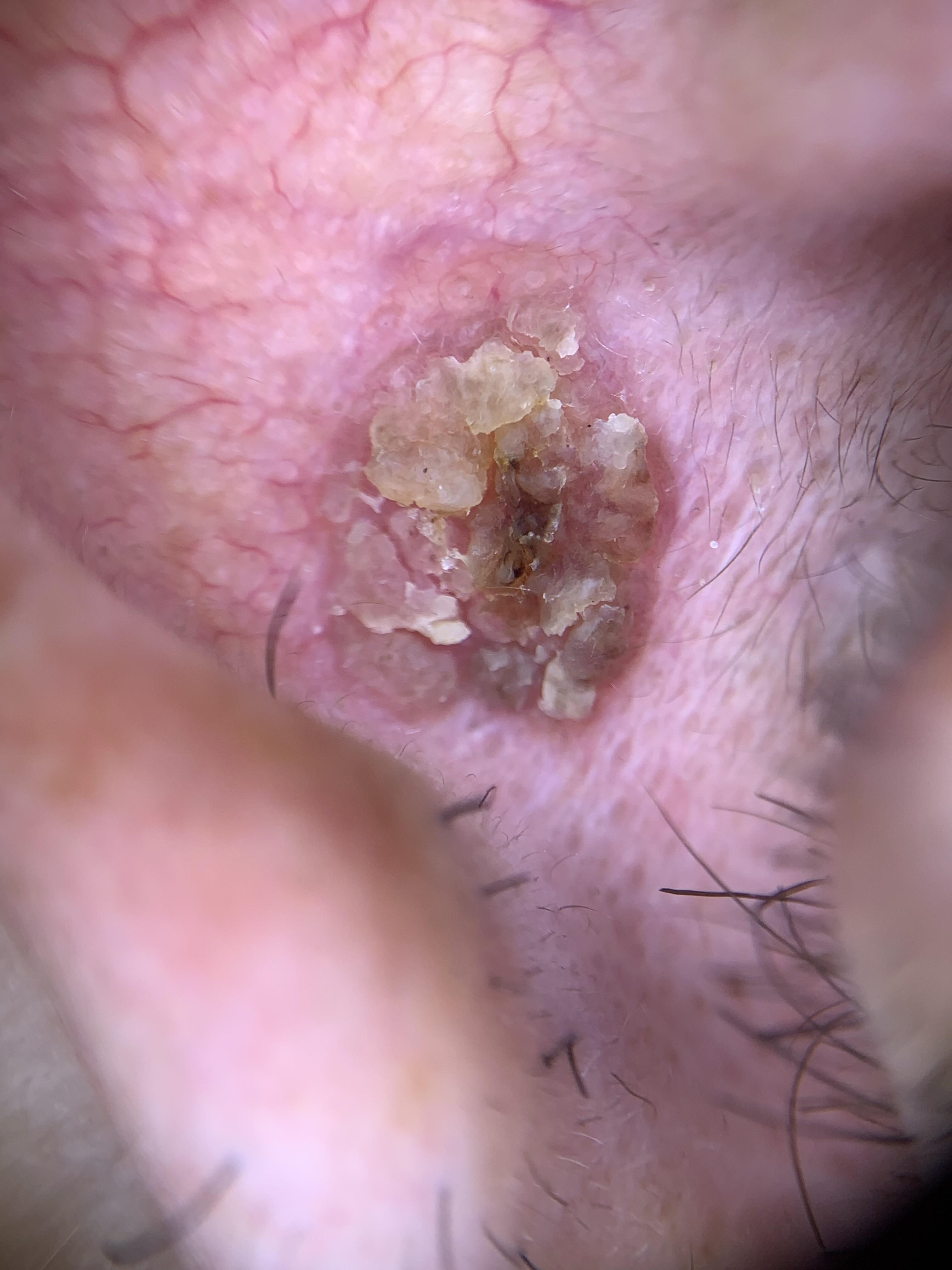patient — male, roughly 60 years of age | anatomic site — the head or neck | diagnosis — Squamous cell carcinoma (biopsy-proven).